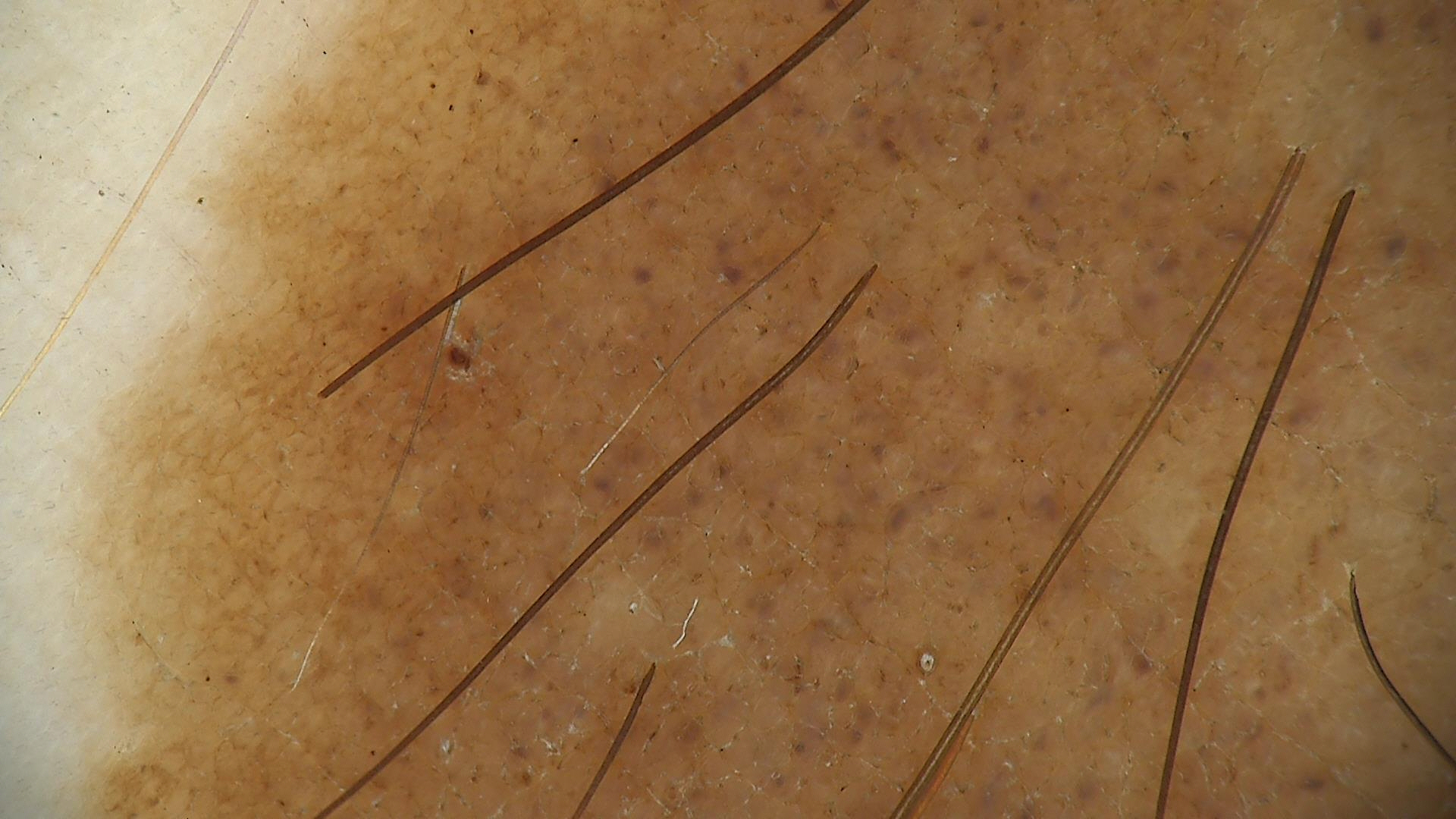Consistent with a congenital compound nevus.